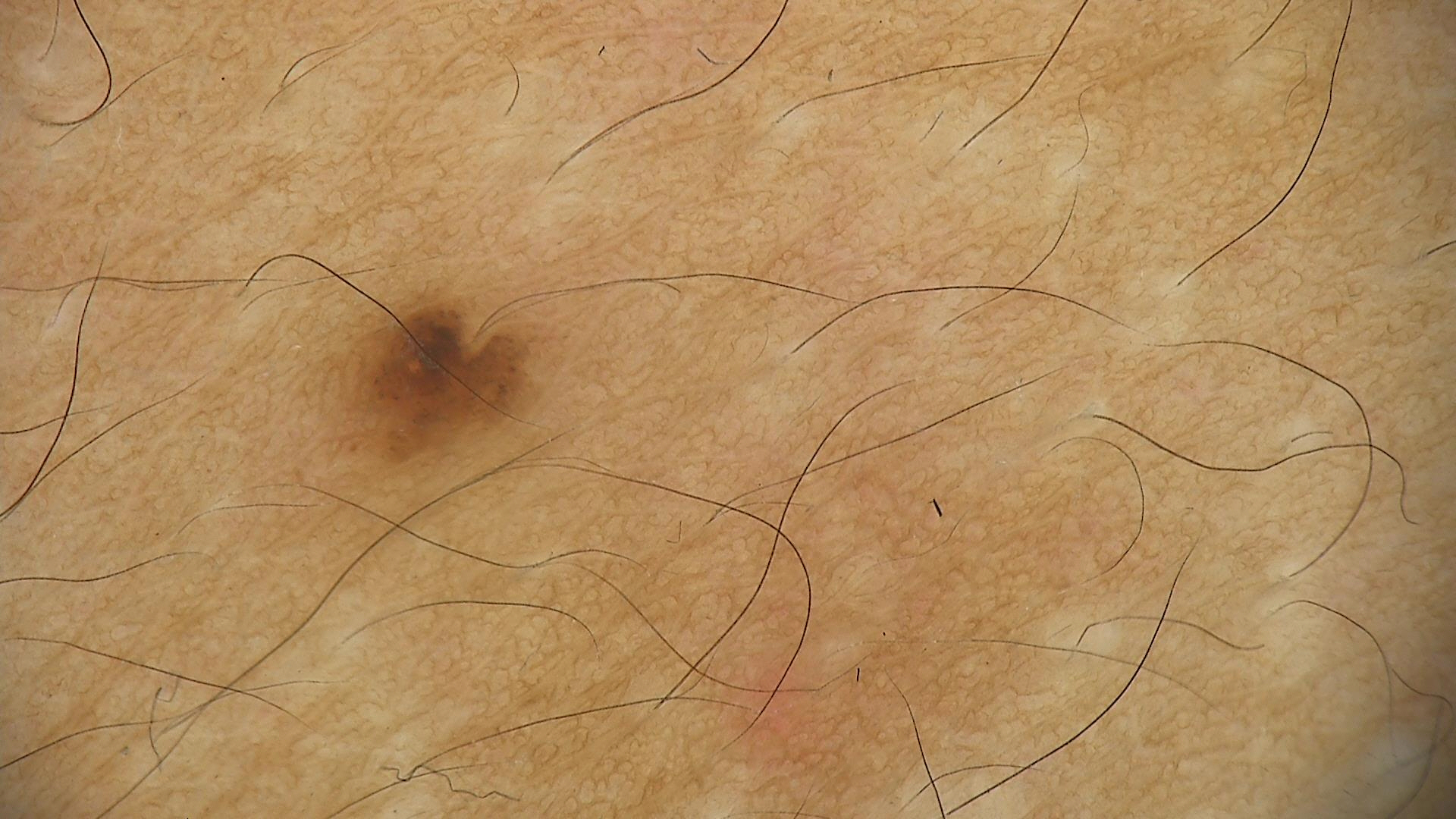A dermoscopy image of a single skin lesion. The diagnosis was a dysplastic junctional nevus.